A close-up photograph · the affected area is the arm.
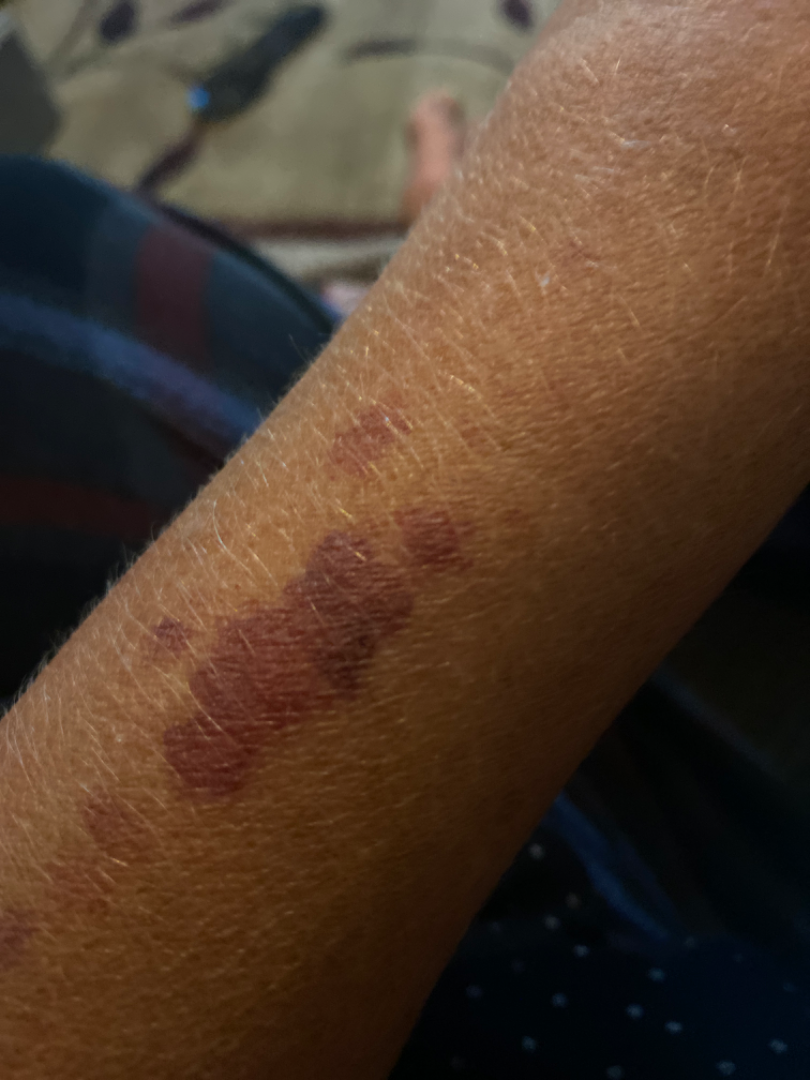described texture=raised or bumpy; reported symptoms=itching; dermatologist impression=ecchymoses (100%).